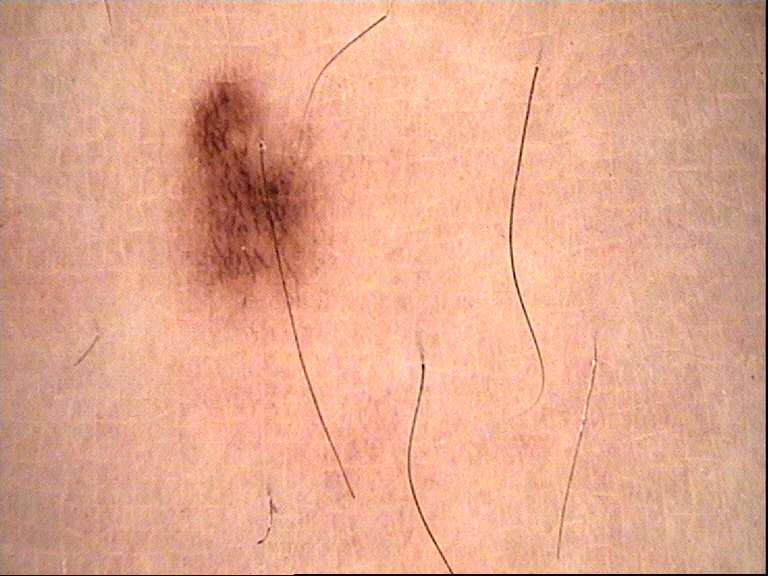Q: What is the diagnosis?
A: dysplastic junctional nevus (expert consensus)